The patient indicates the condition has been present for one to four weeks, the photo was captured at an angle, Fitzpatrick IV, the affected area is the arm, the patient indicates the lesion is rough or flaky:
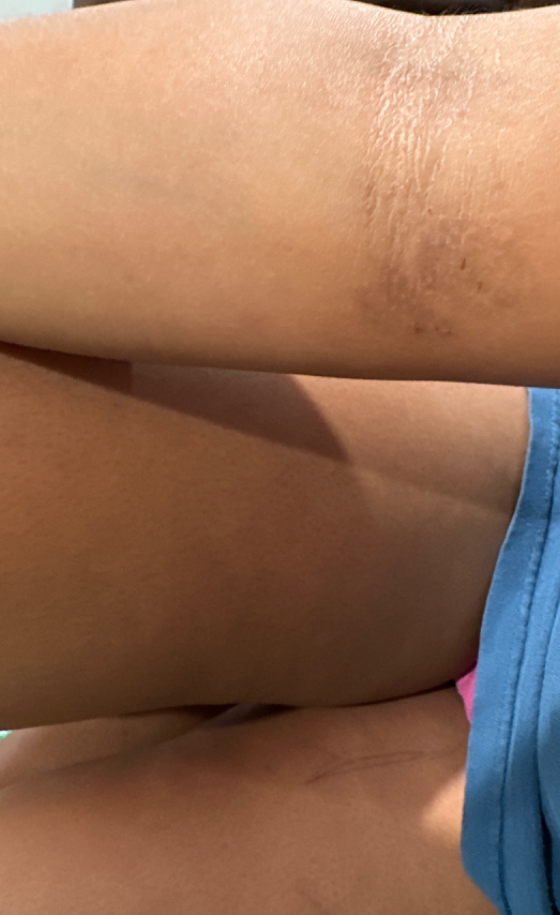<dermatology_case>
  <differential>
    <Eczema>1.0</Eczema>
  </differential>
</dermatology_case>